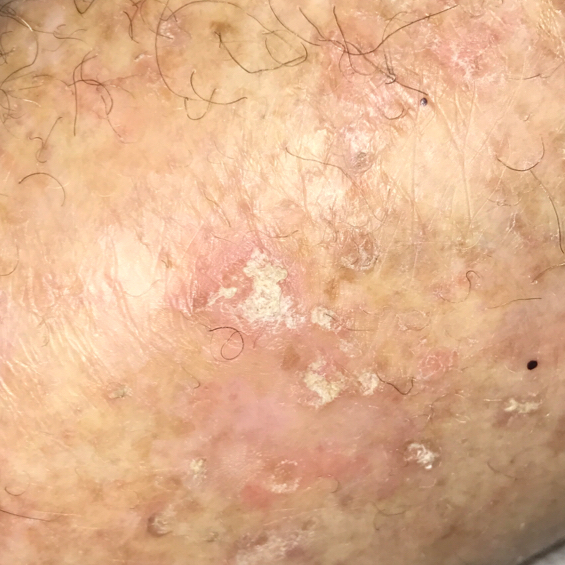A female subject in their early 80s. By history, prior skin cancer (patient or family). A clinical photograph of a skin lesion. The lesion measures approximately 10 × 8 mm. Histopathology confirmed an actinic keratosis.